A dermoscopy image of a single skin lesion. A male patient, in their 70s:
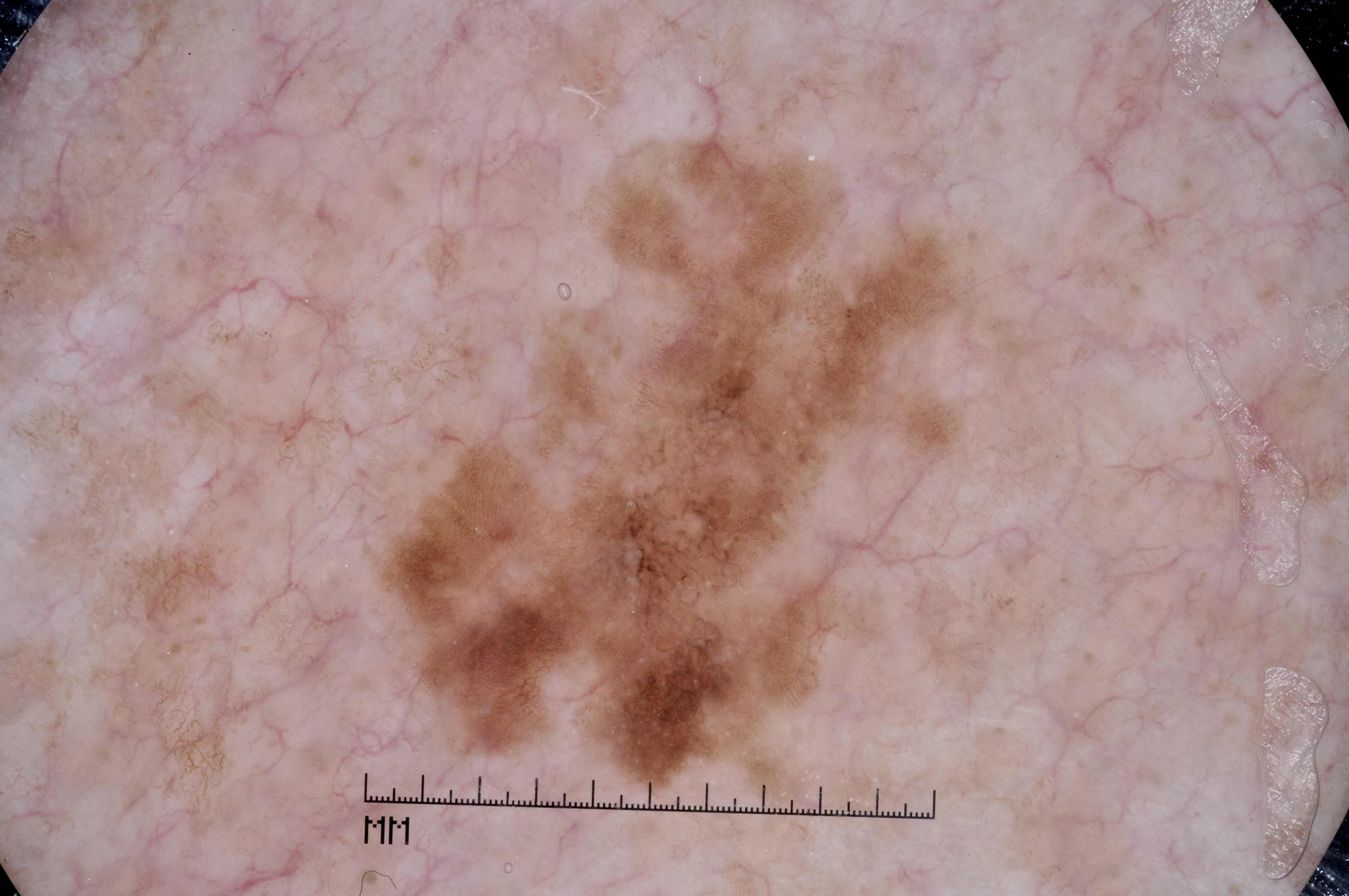The lesion occupies roughly 23% of the field. In (x1, y1, x2, y2) order, the lesion is located at <bbox>339, 26, 1063, 813</bbox>. Dermoscopic assessment notes pigment network and milia-like cysts; no negative network or streaks. Expert review diagnosed this as a melanocytic nevus, a benign lesion.